A dermatoscopic image of a skin lesion.
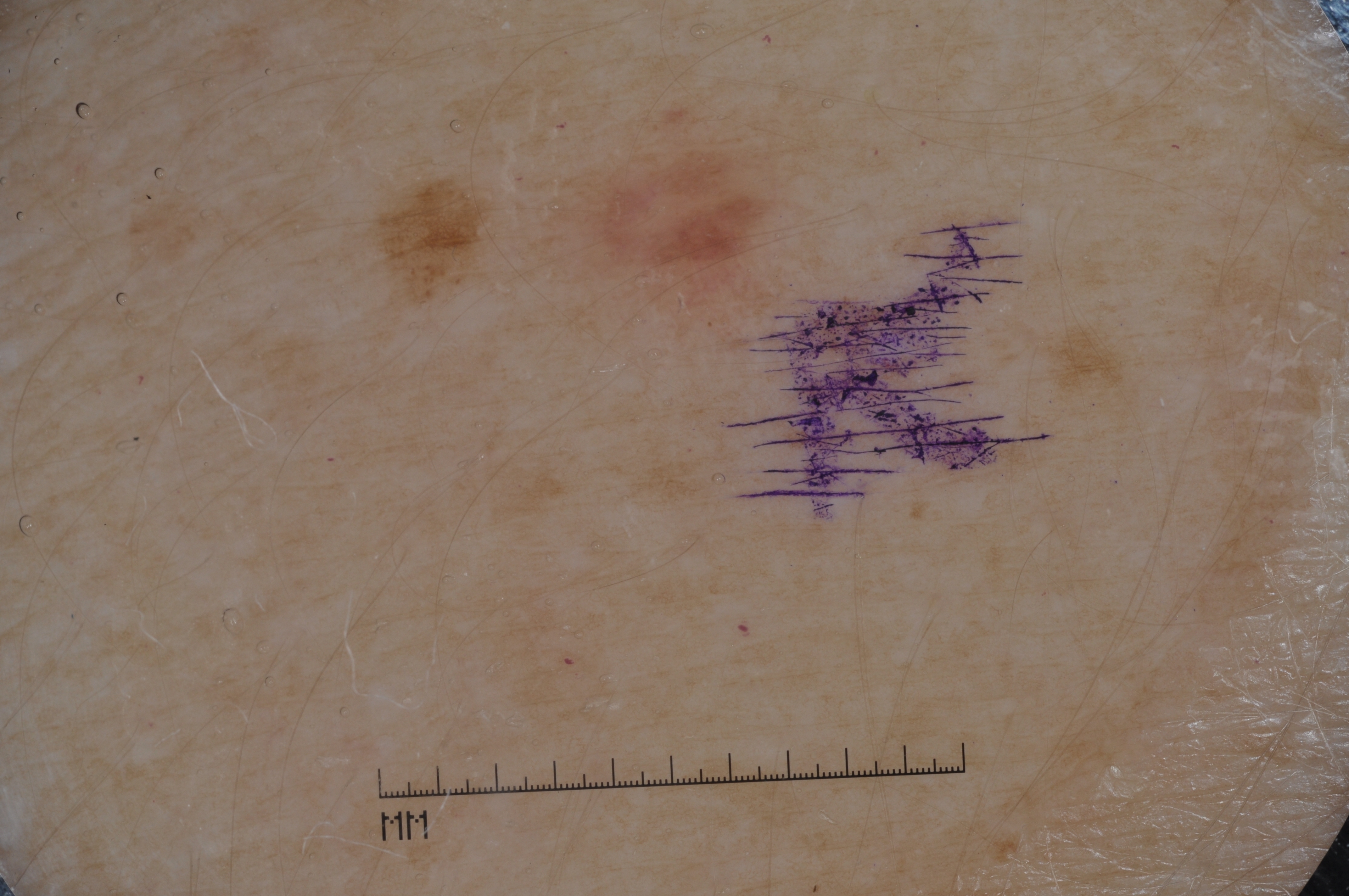- lesion location · 508/123/813/347
- dermoscopic features · milia-like cysts; absent: streaks, pigment network, and negative network
- impression · a melanocytic nevus, a benign skin lesion